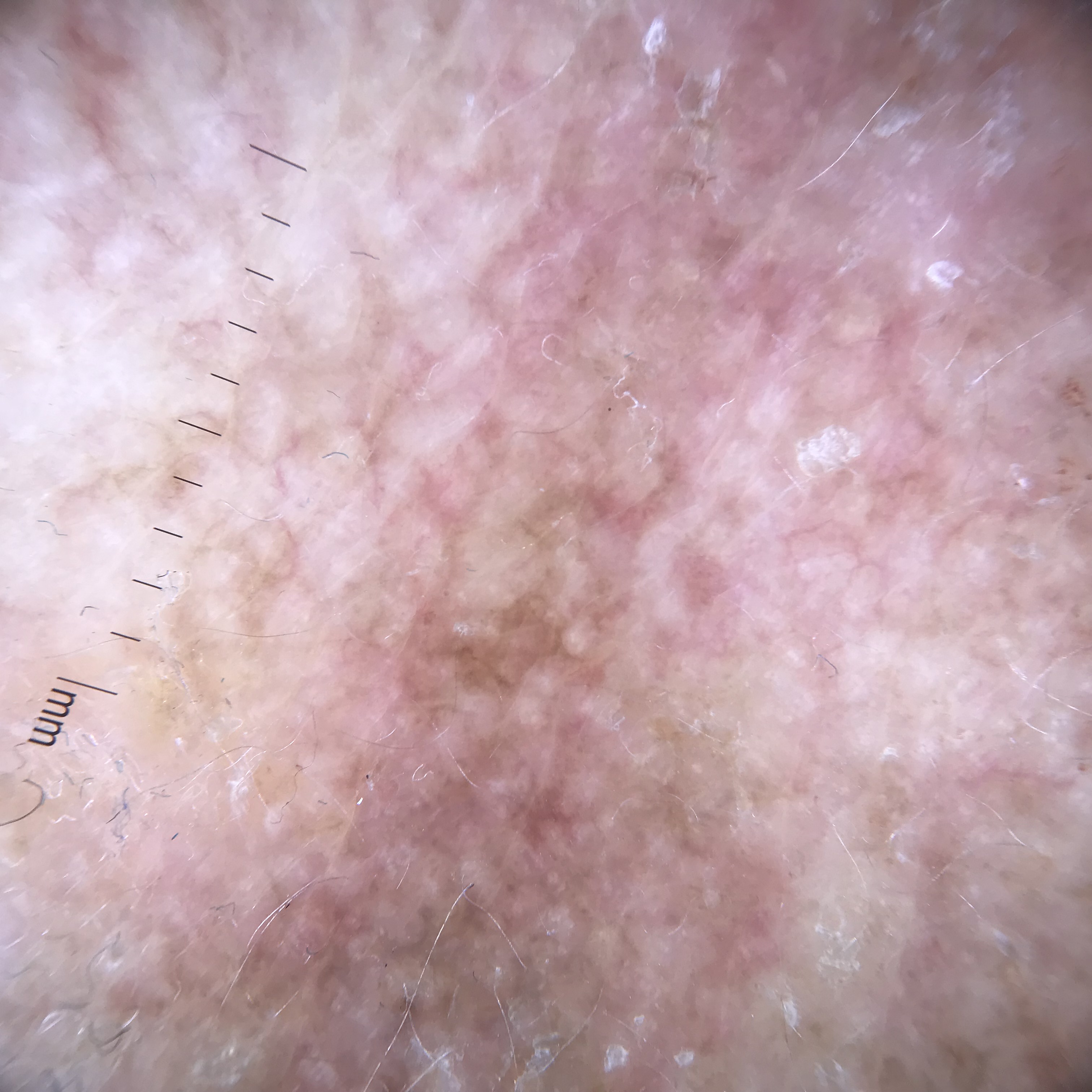Summary: Dermoscopy of a skin lesion. This is a keratinocytic lesion. Conclusion: Consistent with an actinic keratosis.